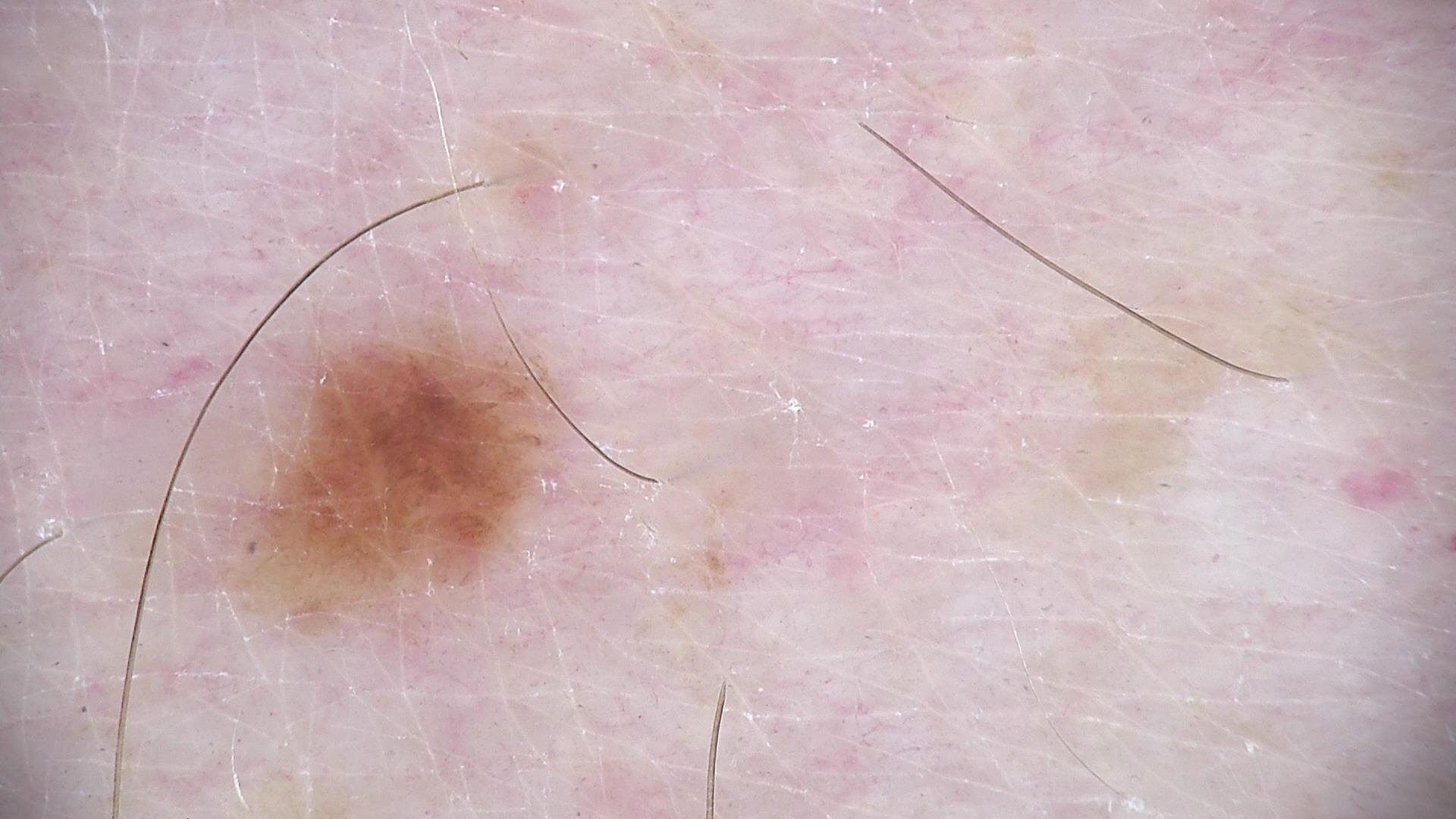A dermoscopic image of a skin lesion.
Consistent with a dysplastic junctional nevus.